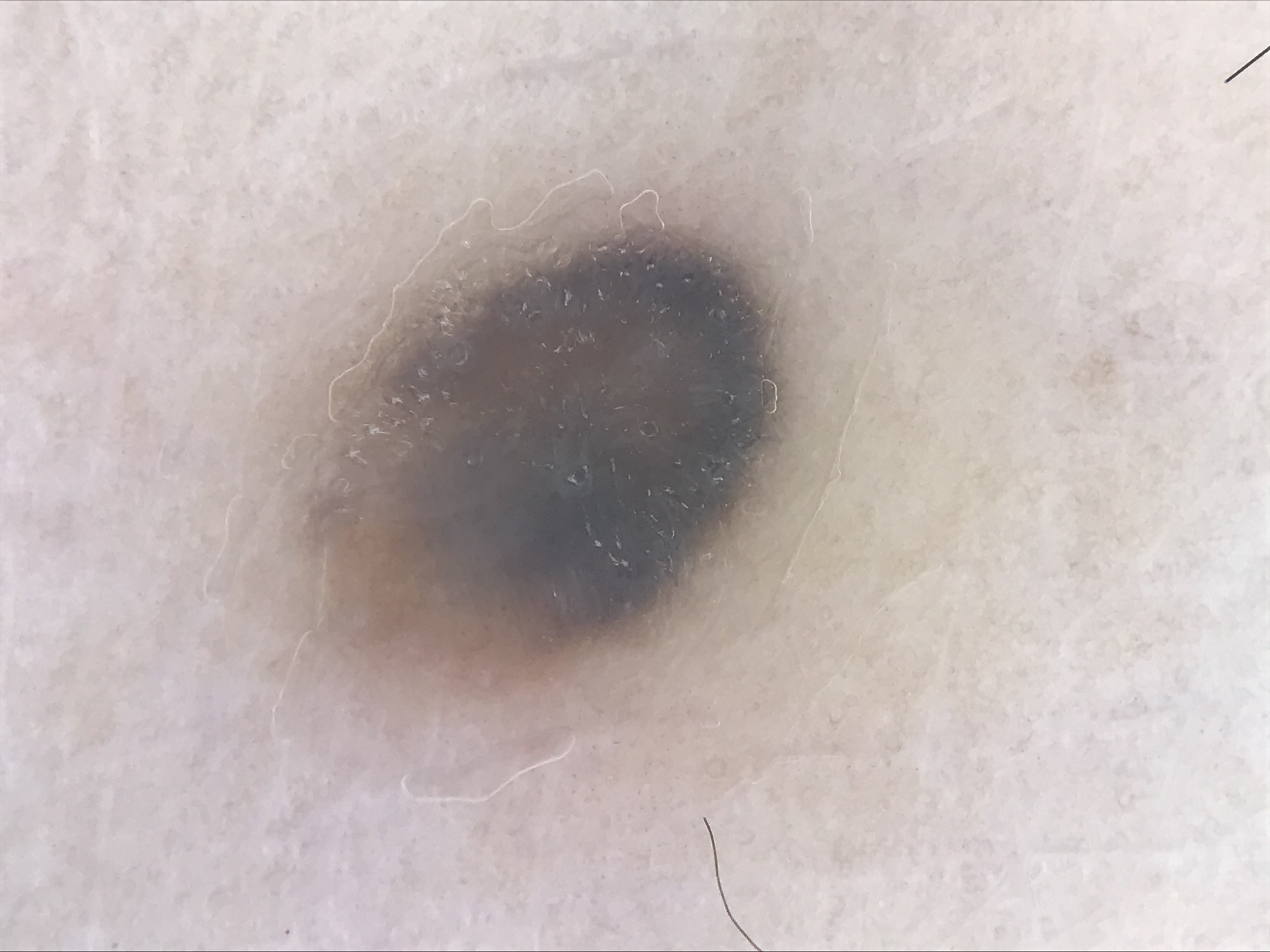A dermoscopic photograph of a skin lesion.
Labeled as a blue nevus.